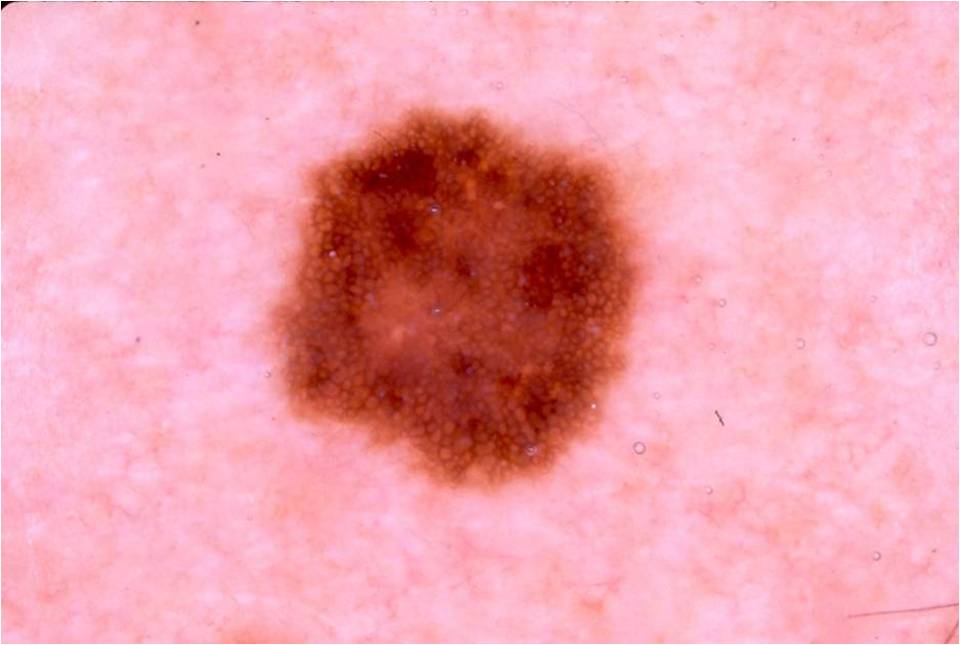Summary: A male patient, aged approximately 75. A skin lesion imaged with a dermatoscope. The visible lesion spans x1=265, y1=103, x2=644, y2=490. On dermoscopy, the lesion shows pigment network, with no negative network, milia-like cysts, streaks, or globules. Conclusion: The diagnostic assessment was a melanocytic nevus.